A clinical photo of a skin lesion taken with a smartphone. A male patient aged 72: 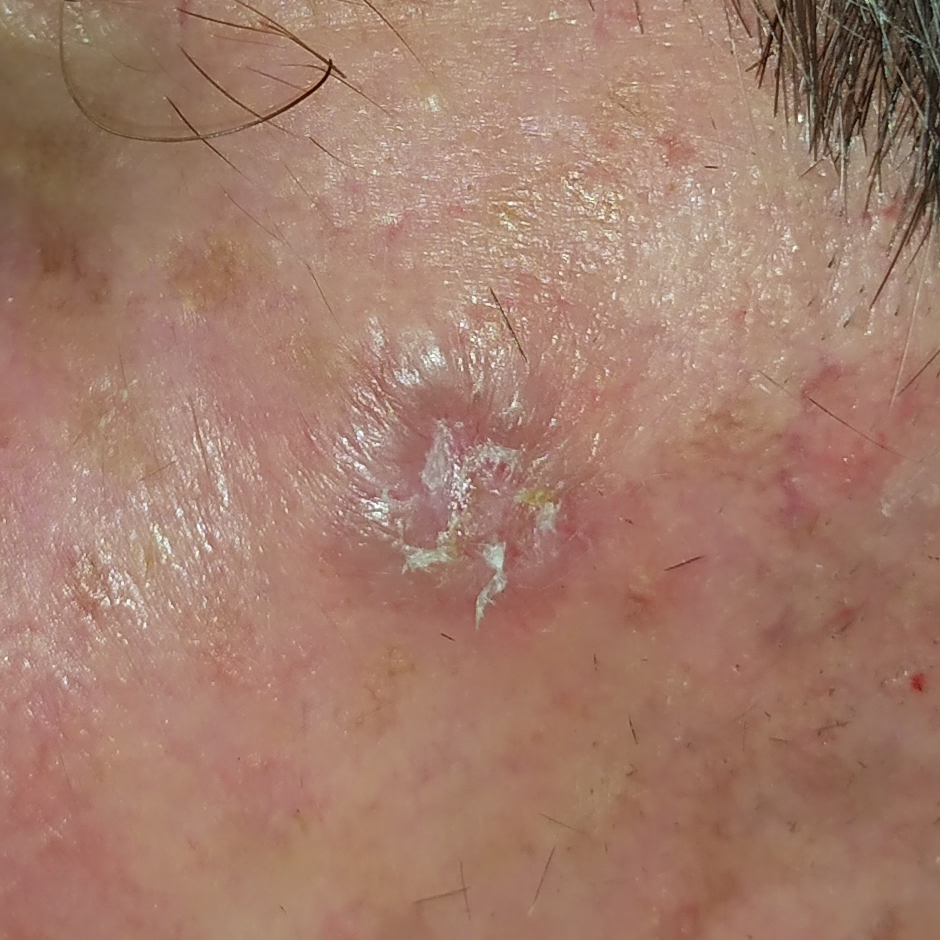Case summary: The lesion was found on the face. The patient describes that the lesion has grown, is elevated, and itches, but has not bled. Diagnosis: Confirmed on histopathology as a basal cell carcinoma.